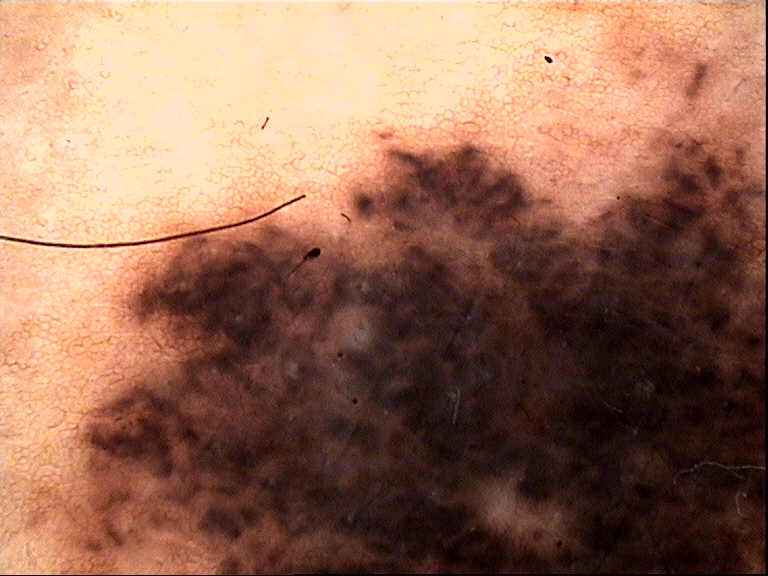lesion type: banal; assessment: congenital compound nevus (expert consensus).